The photo was captured at a distance, the leg is involved: 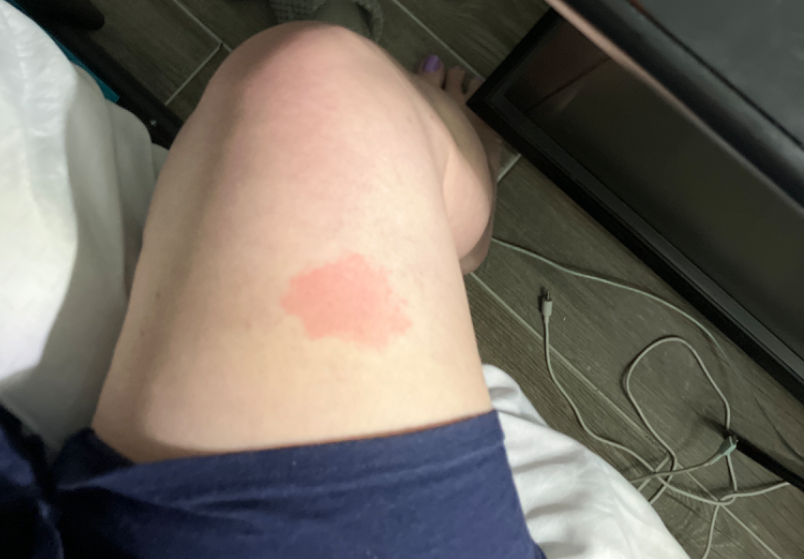Review: The dermatologist could not determine a likely condition from the photograph alone.